The photograph was taken at a distance — 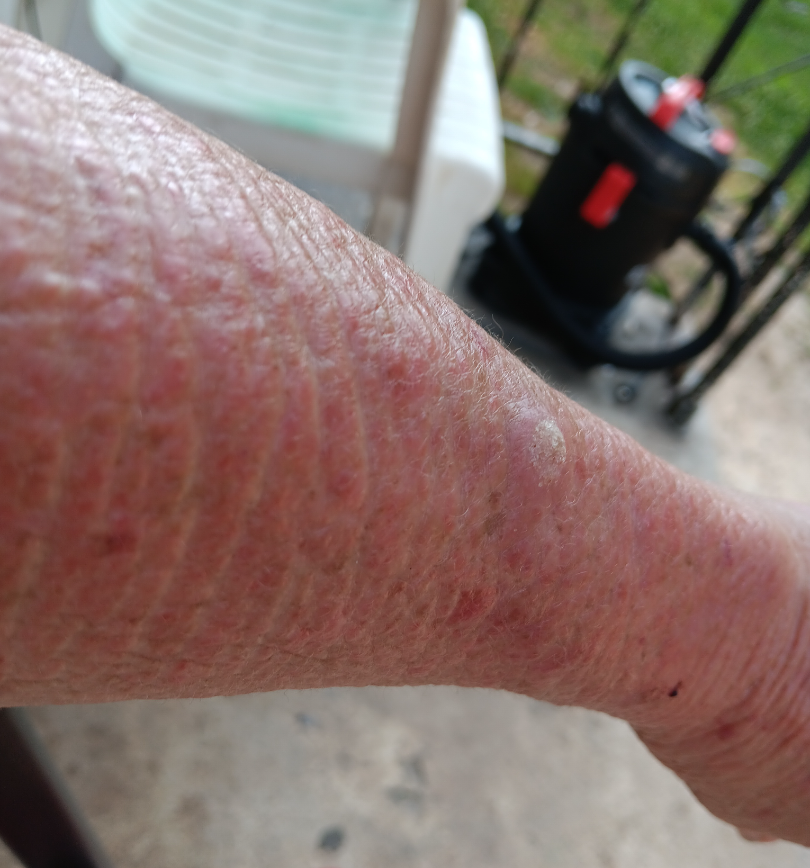In keeping with SCC/SCCIS.